This image was taken at a distance · the affected area is the arm · self-categorized by the patient as a rash · the condition has been present for one to four weeks · the contributor reports the lesion is rough or flaky, fluid-filled and raised or bumpy: 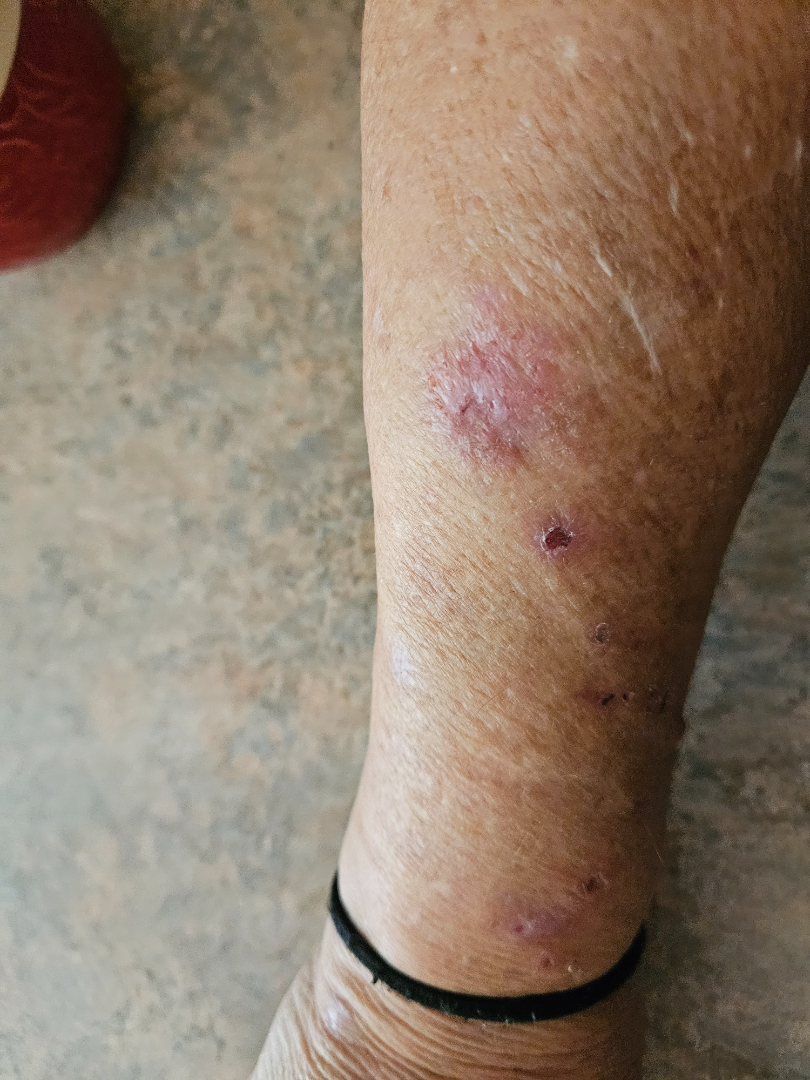Findings:
- assessment: unable to determine